A skin lesion imaged with a dermatoscope.
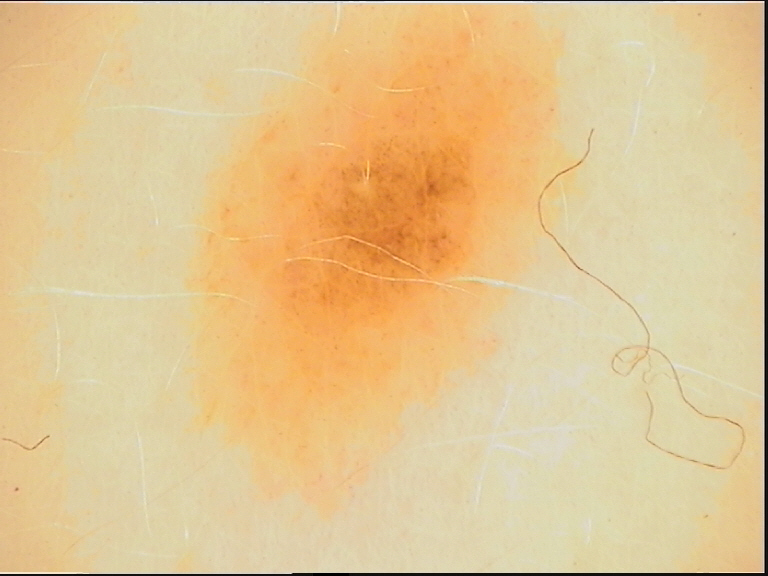Impression: Diagnosed as a dysplastic junctional nevus.